A dermoscopy image of a single skin lesion — 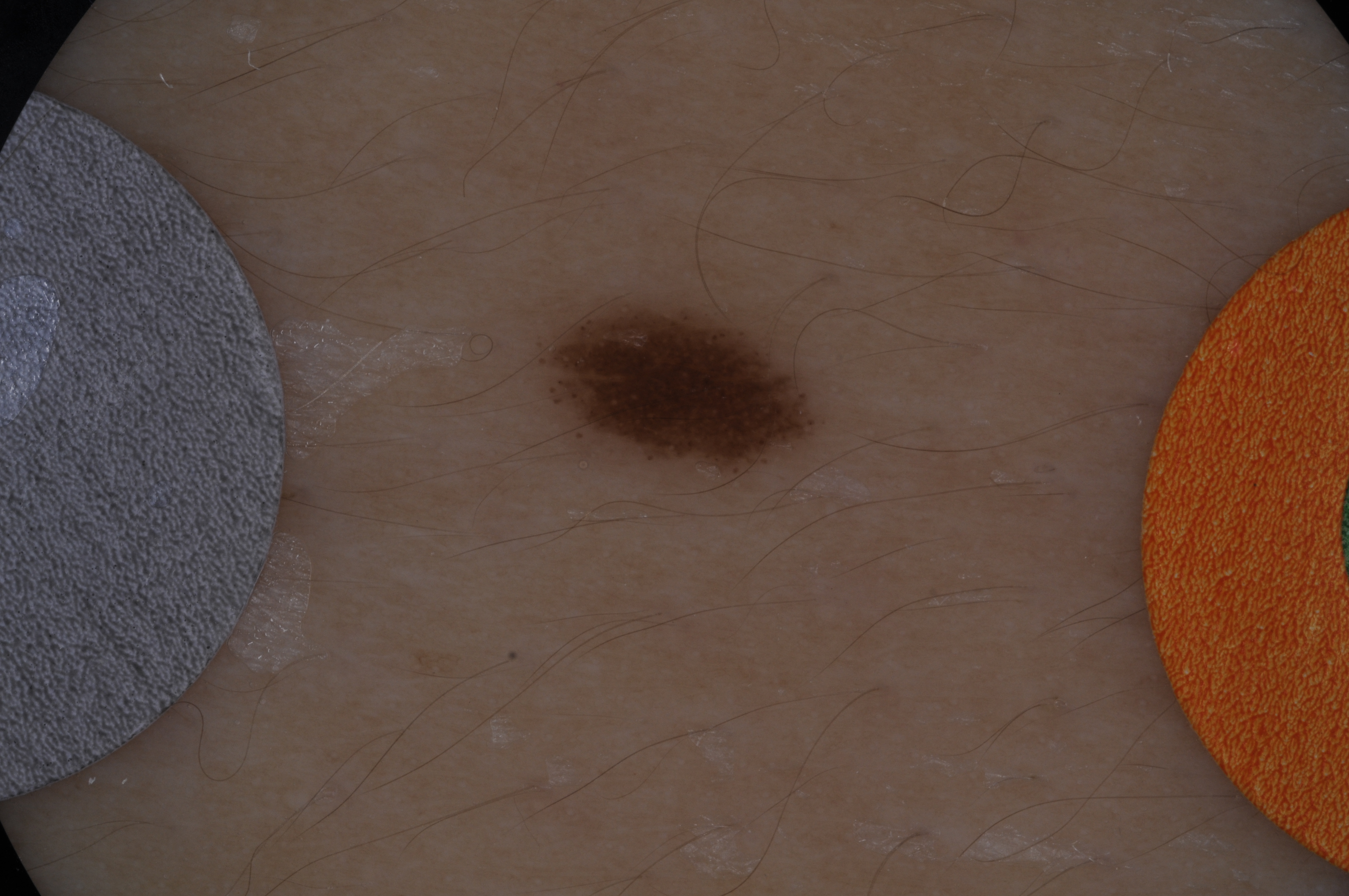location — 532/293/822/485 | absent dermoscopic features — streaks and globules | size — small | impression — a benign lesion.